A dermoscopy image of a single skin lesion:
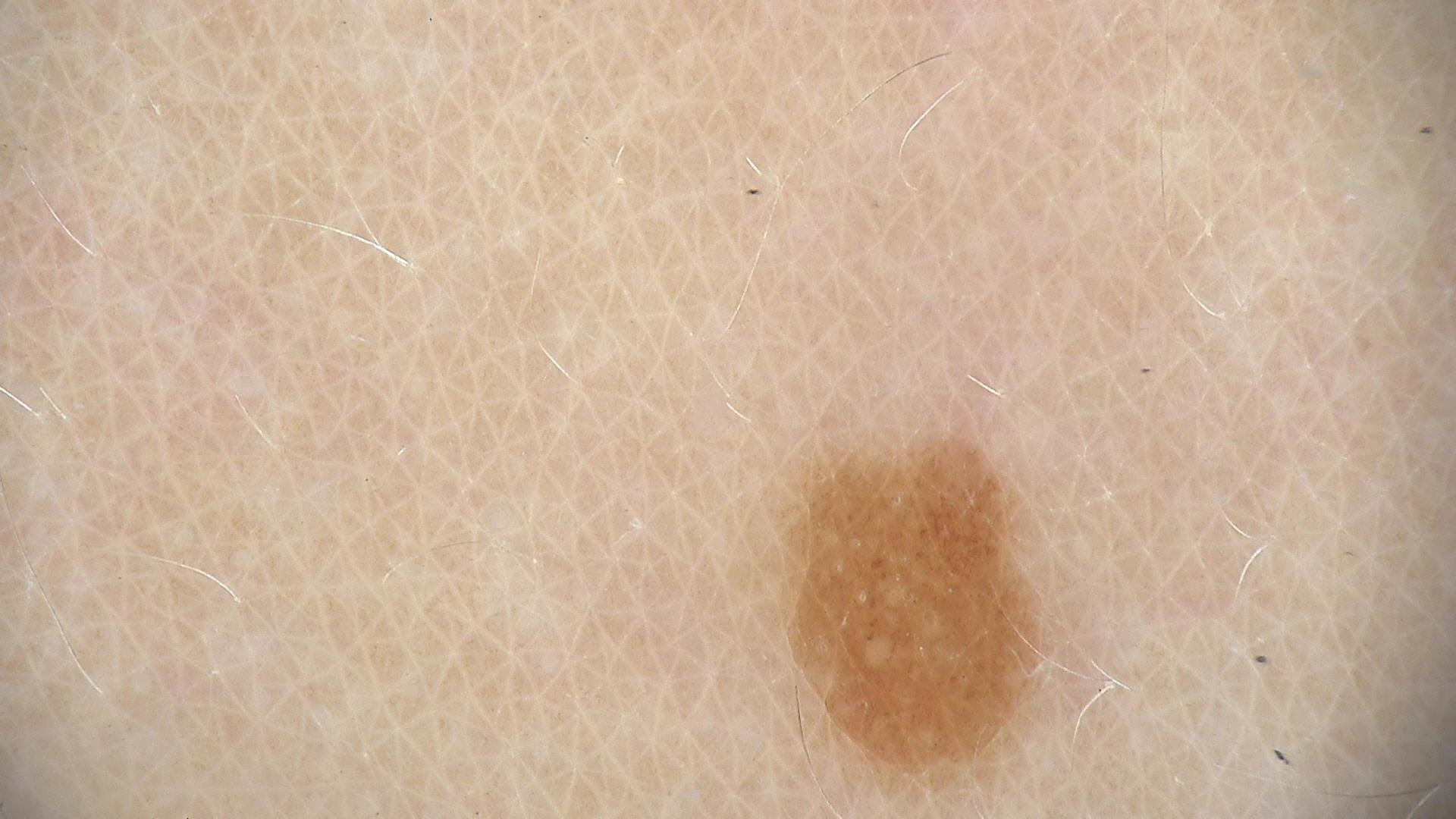Consistent with a benign lesion — a dysplastic junctional nevus.